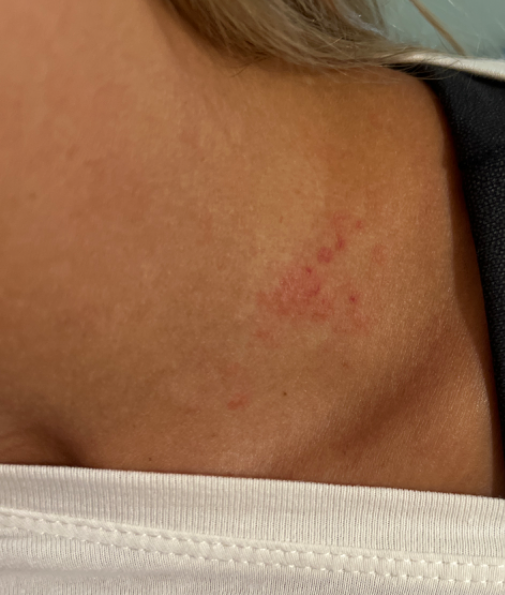{
  "shot_type": "close-up",
  "differential": {
    "Irritant Contact Dermatitis": 1.0
  }
}